By self-report, a family history of skin cancer, a personal history of skin cancer, a personal history of cancer, no sunbed use, and no immunosuppression. A dermoscopy image of a skin lesion. The patient says their skin reddens with sun exposure.
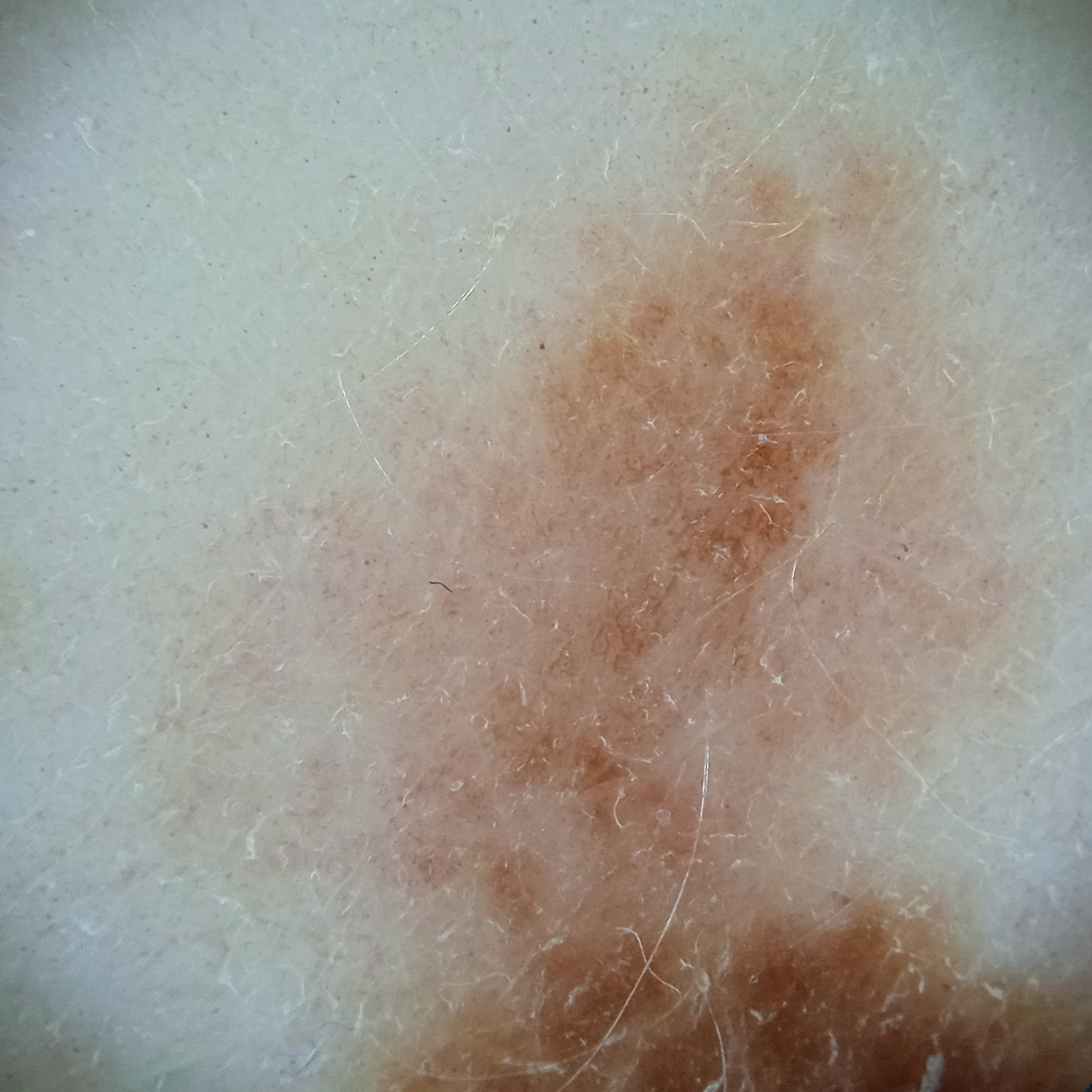Case summary:
The lesion is on the torso. The lesion is about 17.5 mm across.
Assessment:
The consensus diagnosis for this lesion was a melanoma.